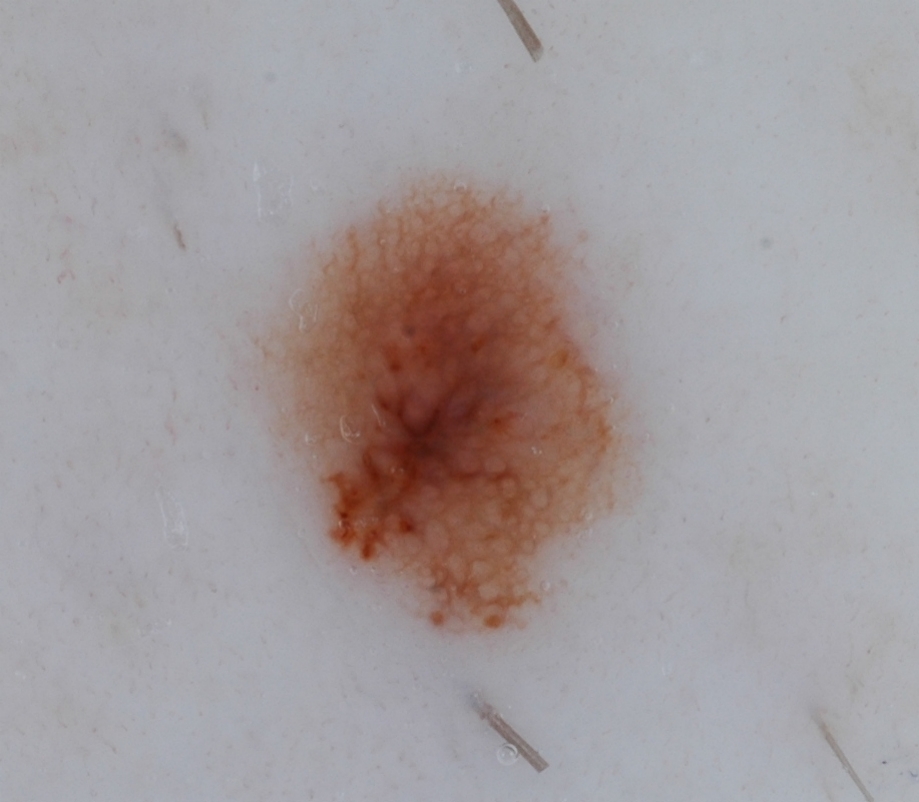Findings: A dermoscopy image of a single skin lesion. A mid-sized lesion within the field. The lesion is located at [243,168,641,648]. Dermoscopic examination shows globules and pigment network, with no negative network, streaks, or milia-like cysts. Assessment: Expert review diagnosed this as a melanocytic nevus, a benign lesion.